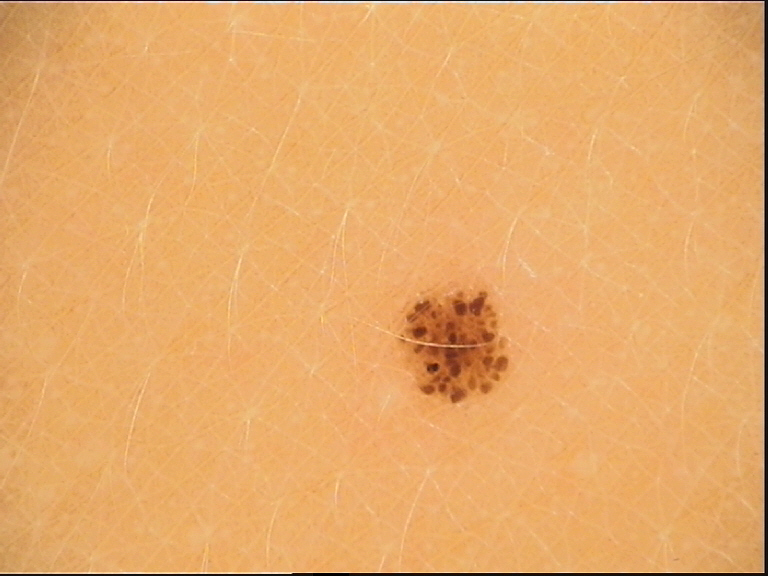Consistent with a junctional nevus.